By history, prior skin cancer (patient or family) and pesticide exposure; a male subject in their 60s; the patient was assessed as skin type III; a clinical close-up photograph of a skin lesion: 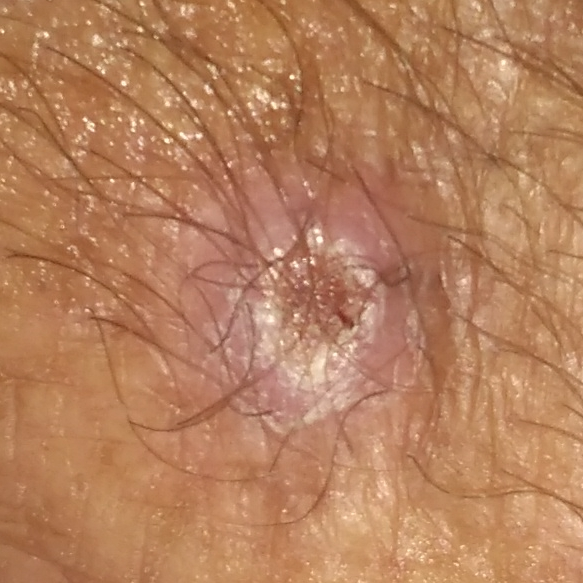location: a hand
diameter: 10x9 mm
patient-reported symptoms: itching, elevation, bleeding, growth
pathology: basal cell carcinoma (biopsy-proven)